A female subject about 50 years old; contact-polarized dermoscopy of a skin lesion: 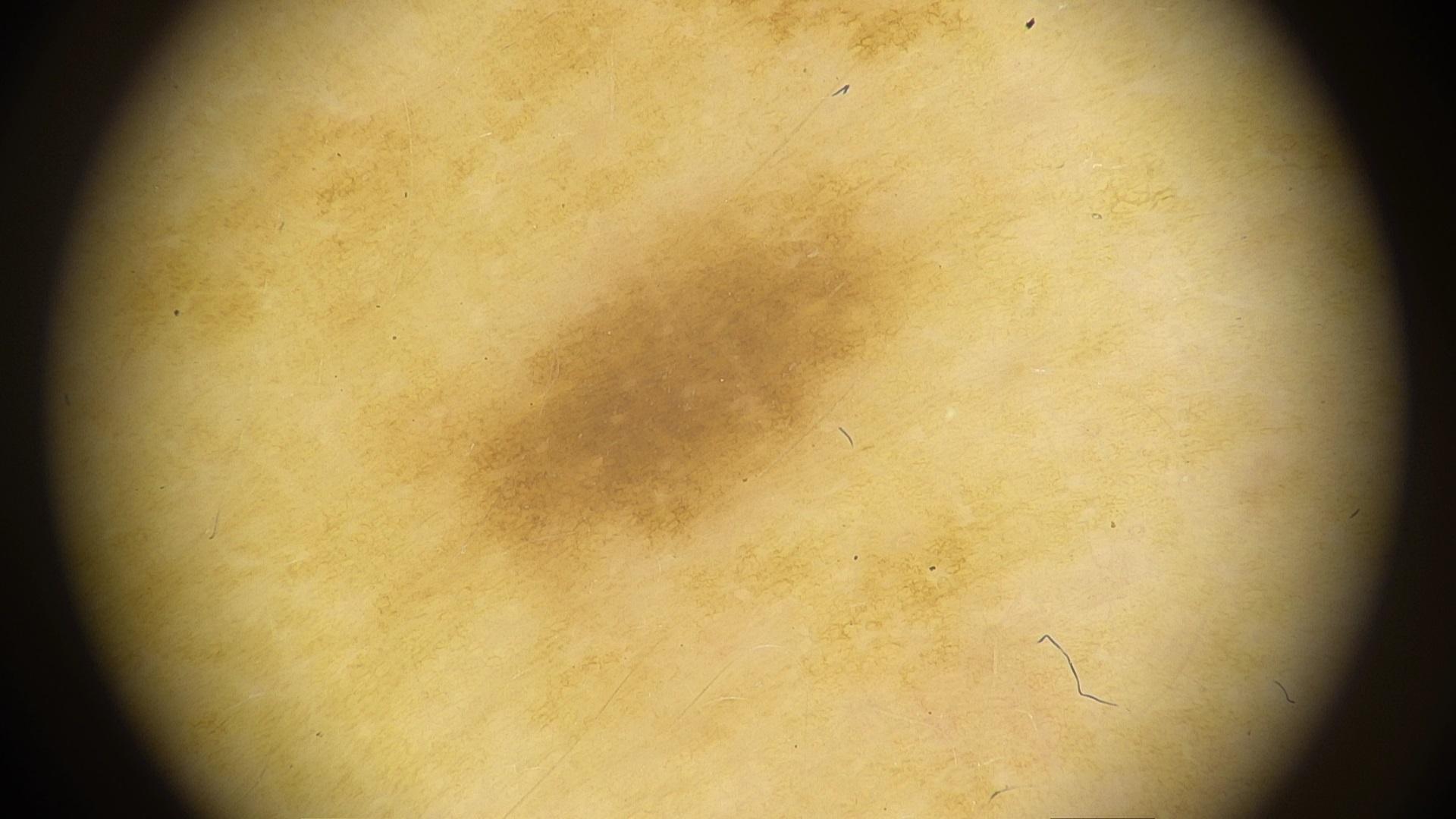{
  "lesion_location": {
    "region": "an upper extremity"
  },
  "diagnosis": {
    "name": "Nevus",
    "malignancy": "benign",
    "confirmation": "expert clinical impression",
    "lineage": "melanocytic"
  }
}